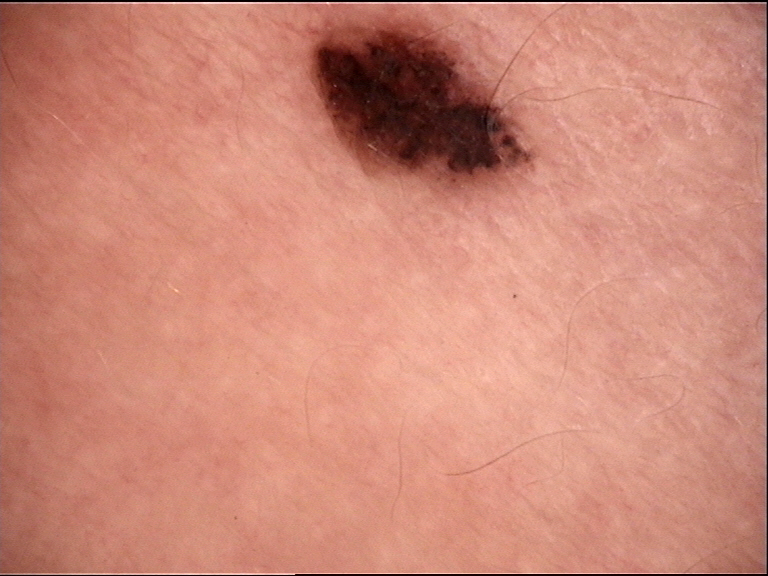The diagnosis was a dysplastic junctional nevus.